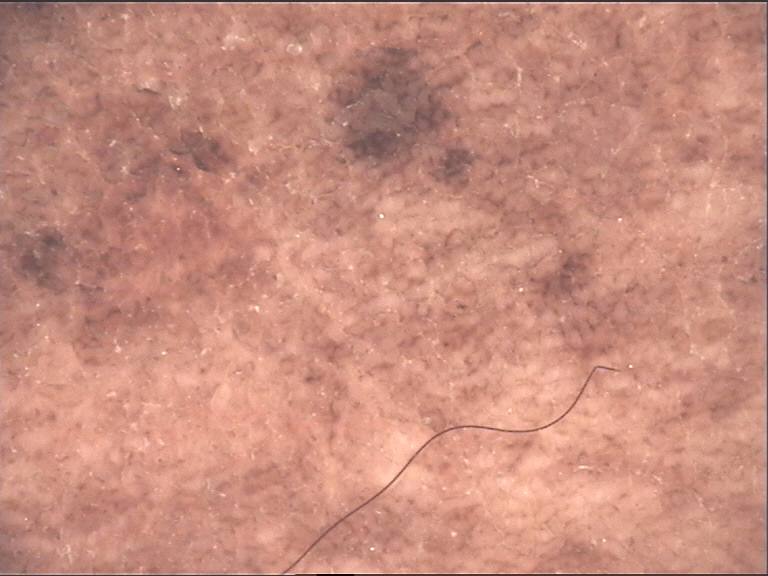Classified as a congenital compound nevus.